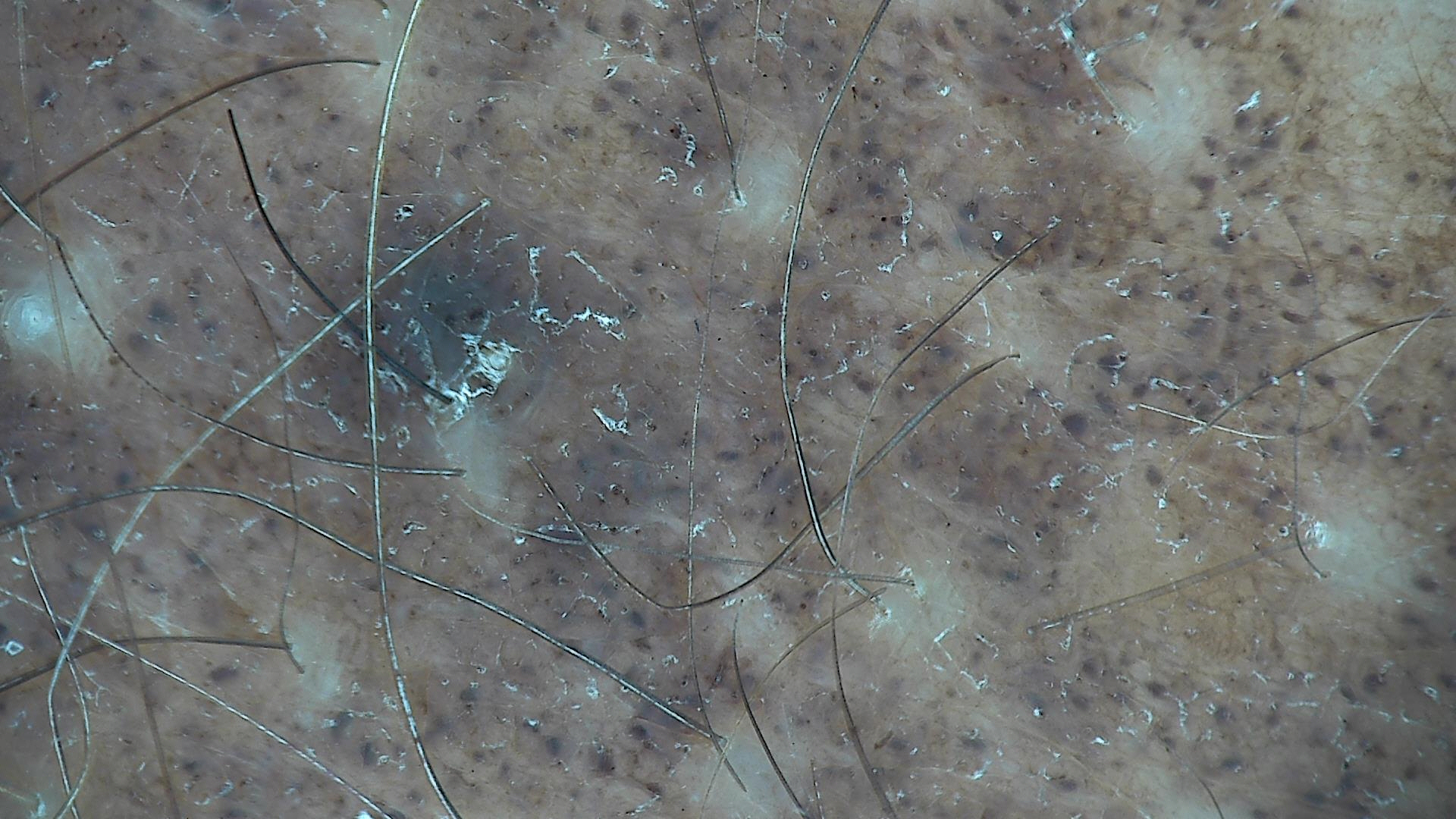modality — dermatoscopy; lesion type — banal; class — congenital compound nevus (expert consensus).